A skin lesion imaged with a dermatoscope · acquired for a research image collection, with no referral diagnosis · a male patient aged 72:
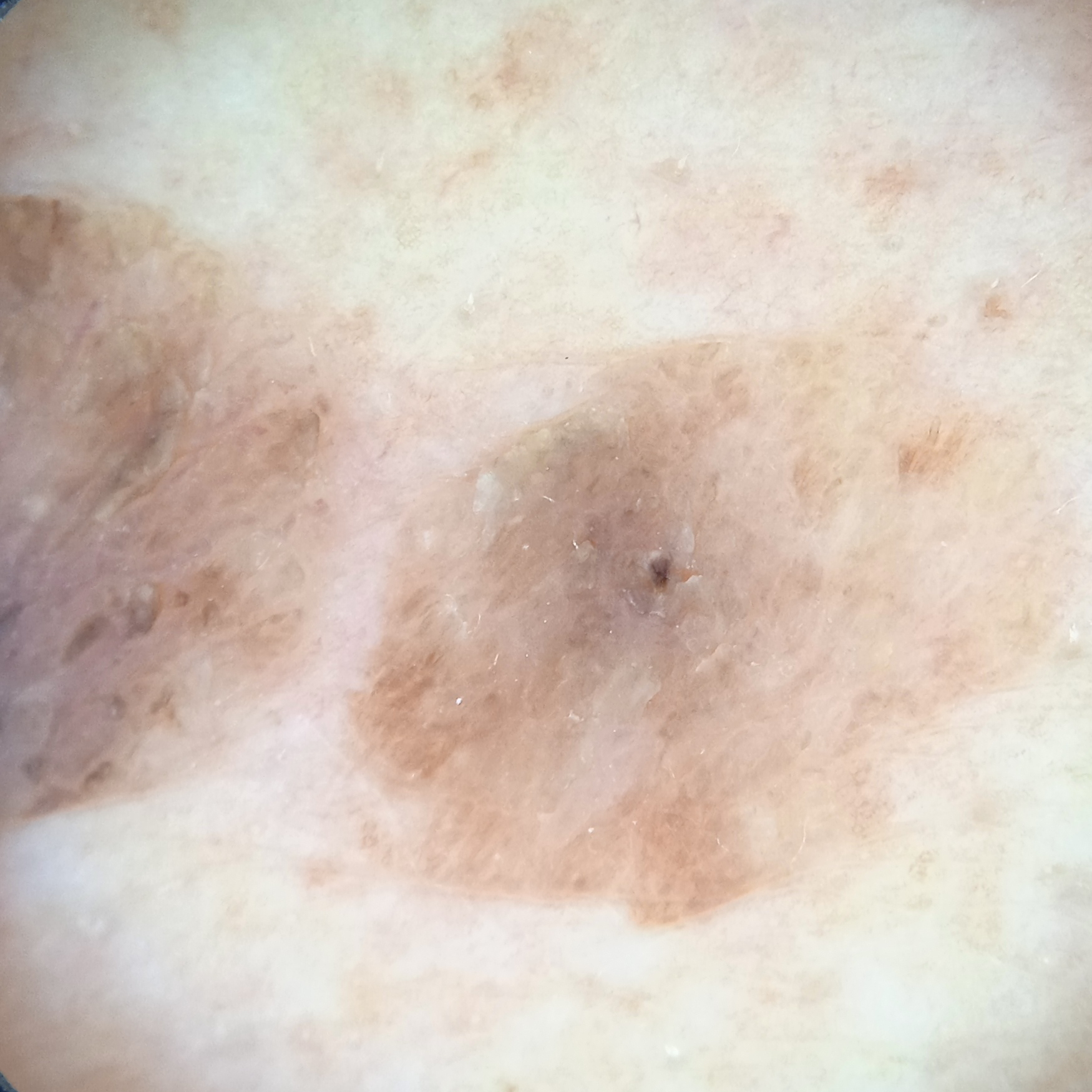The lesion is on the back. The lesion measures approximately 12.8 mm. The consensus diagnosis for this lesion was a seborrheic keratosis.